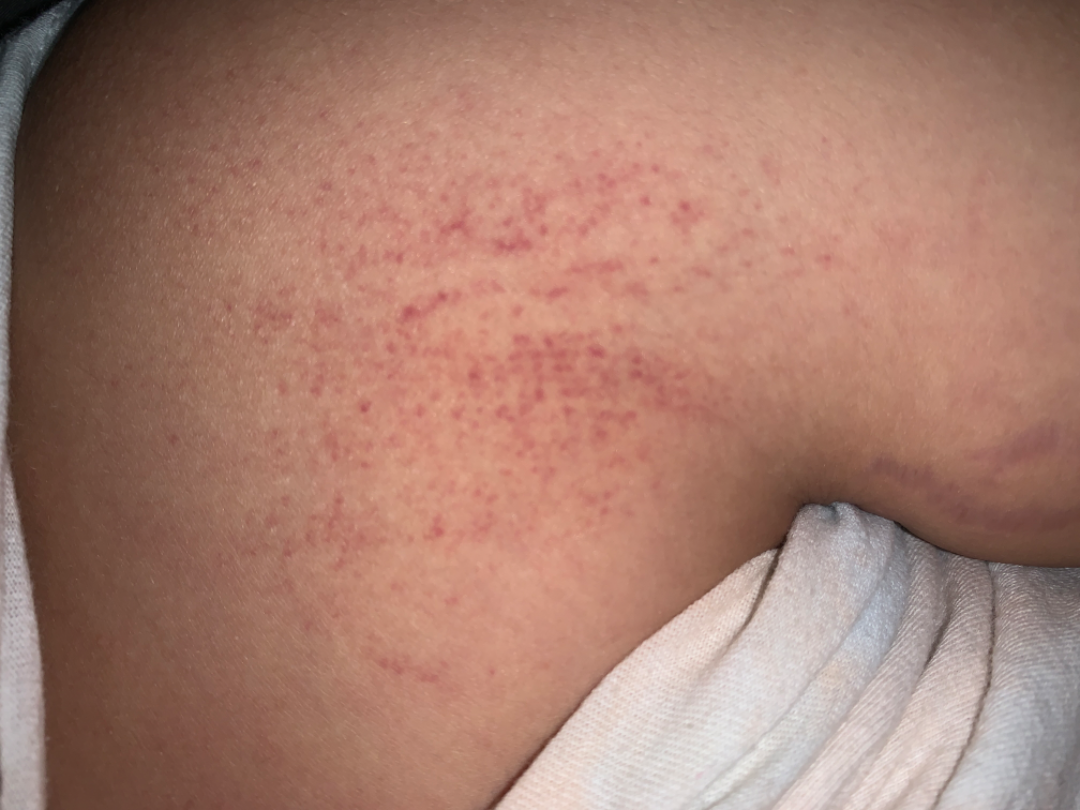The skin condition could not be confidently assessed from this image.
A close-up photograph.
The patient described the issue as a rash.
The subject is 18–29, female.
Symptoms reported: enlargement and itching.
The affected area is the arm.